A dermoscopy image of a single skin lesion.
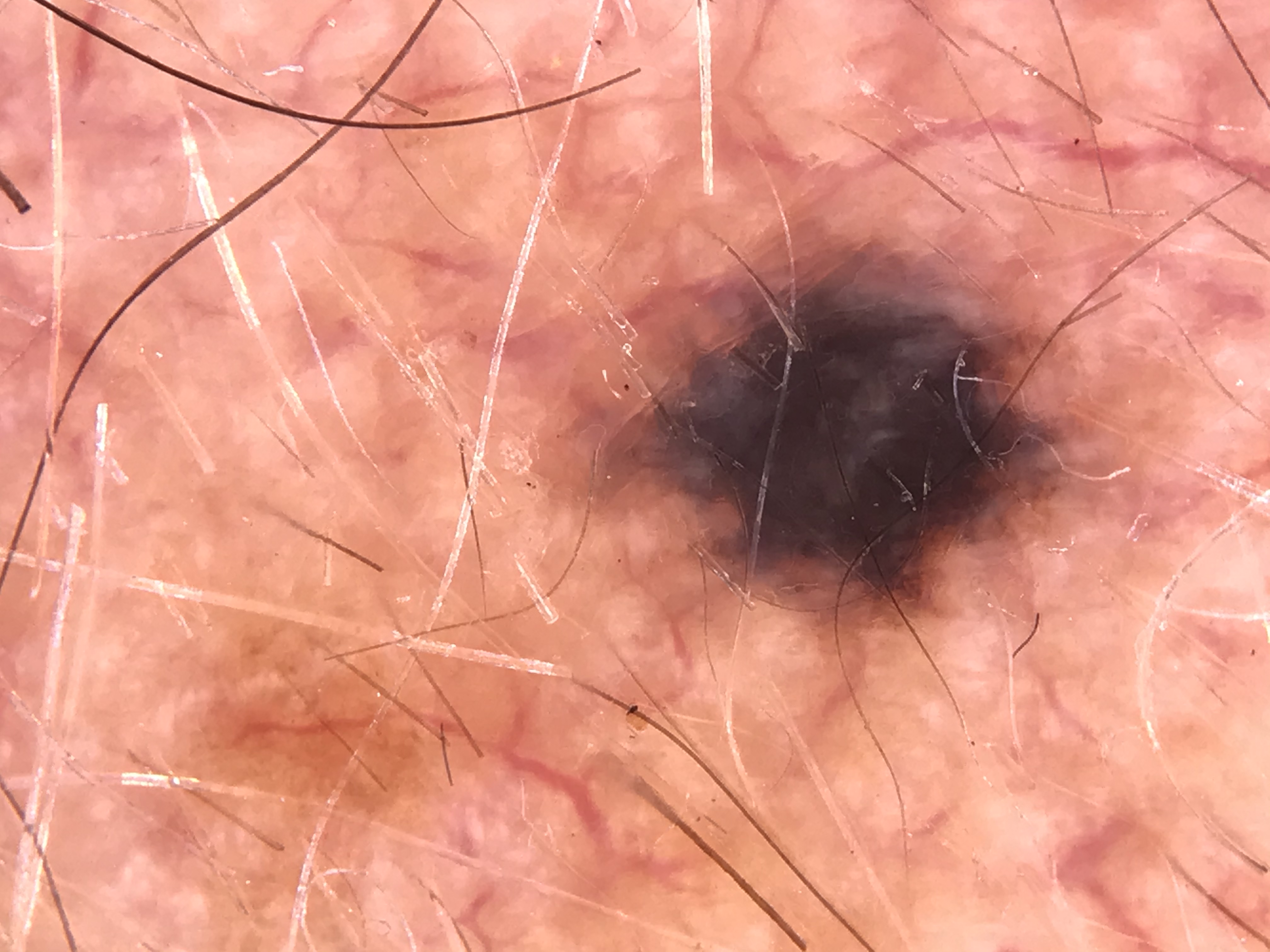class: blue nevus (expert consensus).